The contributor is a female aged 60–69, the lesion is described as fluid-filled, self-categorized by the patient as a rash, the arm and back of the hand are involved, the photo was captured at a distance, no relevant systemic symptoms, the patient notes the condition has been present for more than five years, the patient notes bleeding and bothersome appearance:
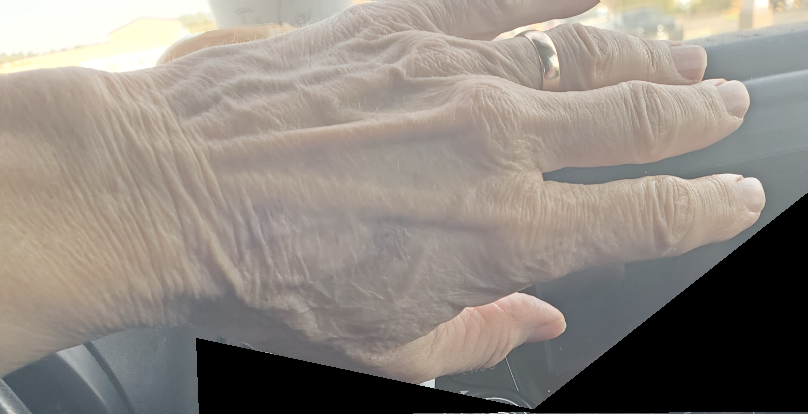<case>
<differential>
  <leading>ecchymoses</leading>
</differential>
</case>